This is a close-up image. Texture is reported as flat. The condition has been present for about one day. The leg and arm are involved.
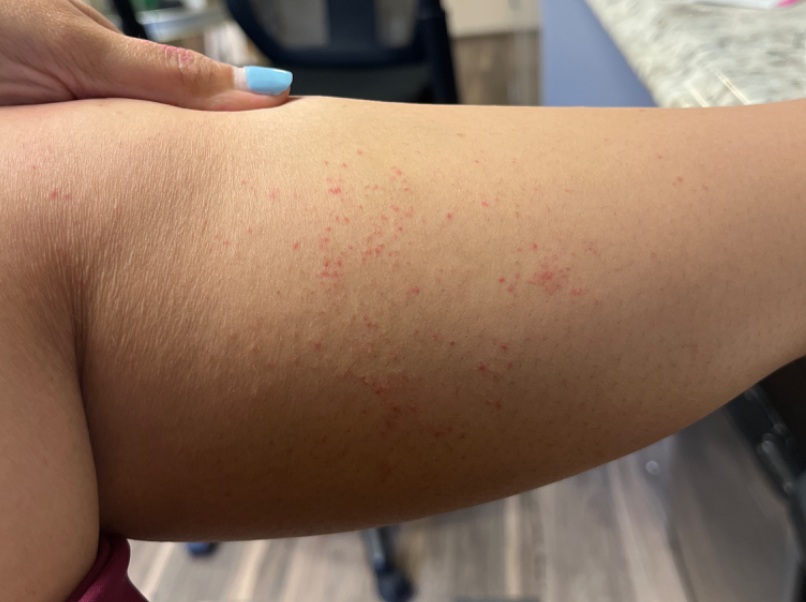{
  "differential": {
    "tied_lead": [
      "Pigmented purpuric eruption",
      "Eczema",
      "Allergic Contact Dermatitis"
    ]
  }
}